A dermoscopic close-up of a skin lesion.
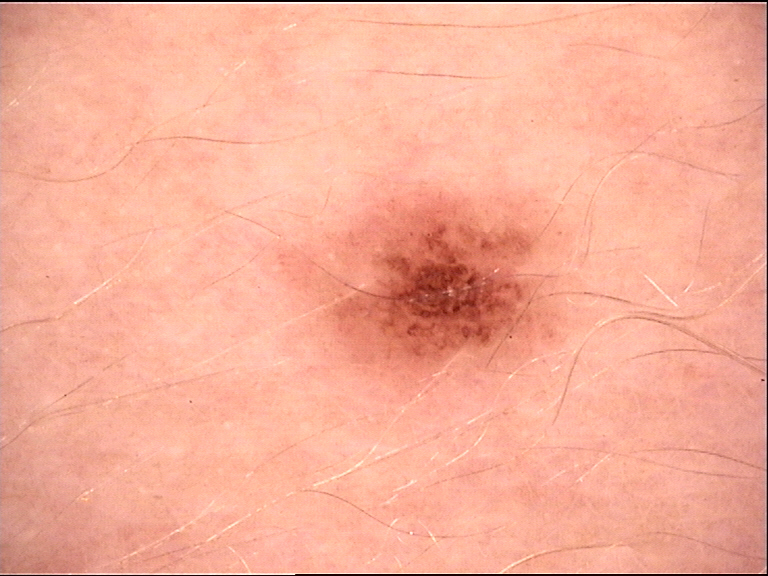The architecture is that of a banal lesion. Consistent with a junctional nevus.